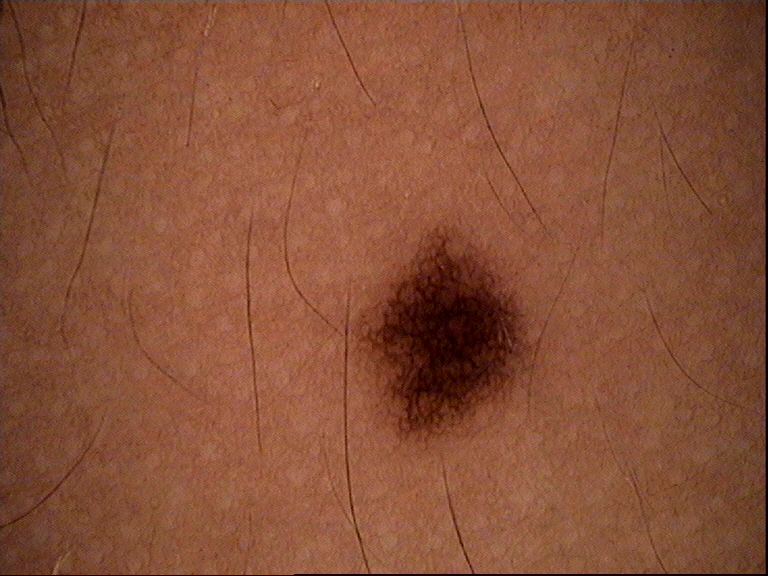class=dysplastic junctional nevus (expert consensus).